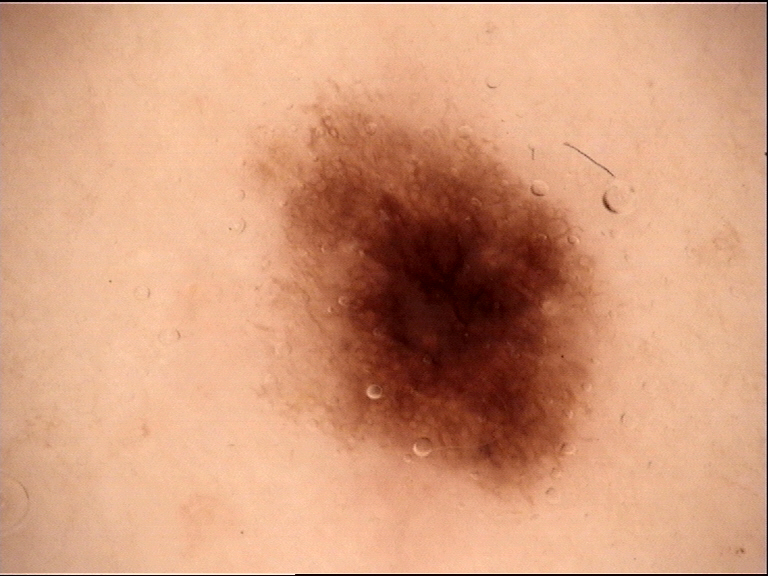A dermatoscopic image of a skin lesion. The diagnosis was a benign lesion — a dysplastic junctional nevus.